This is a dermoscopic photograph of a skin lesion — 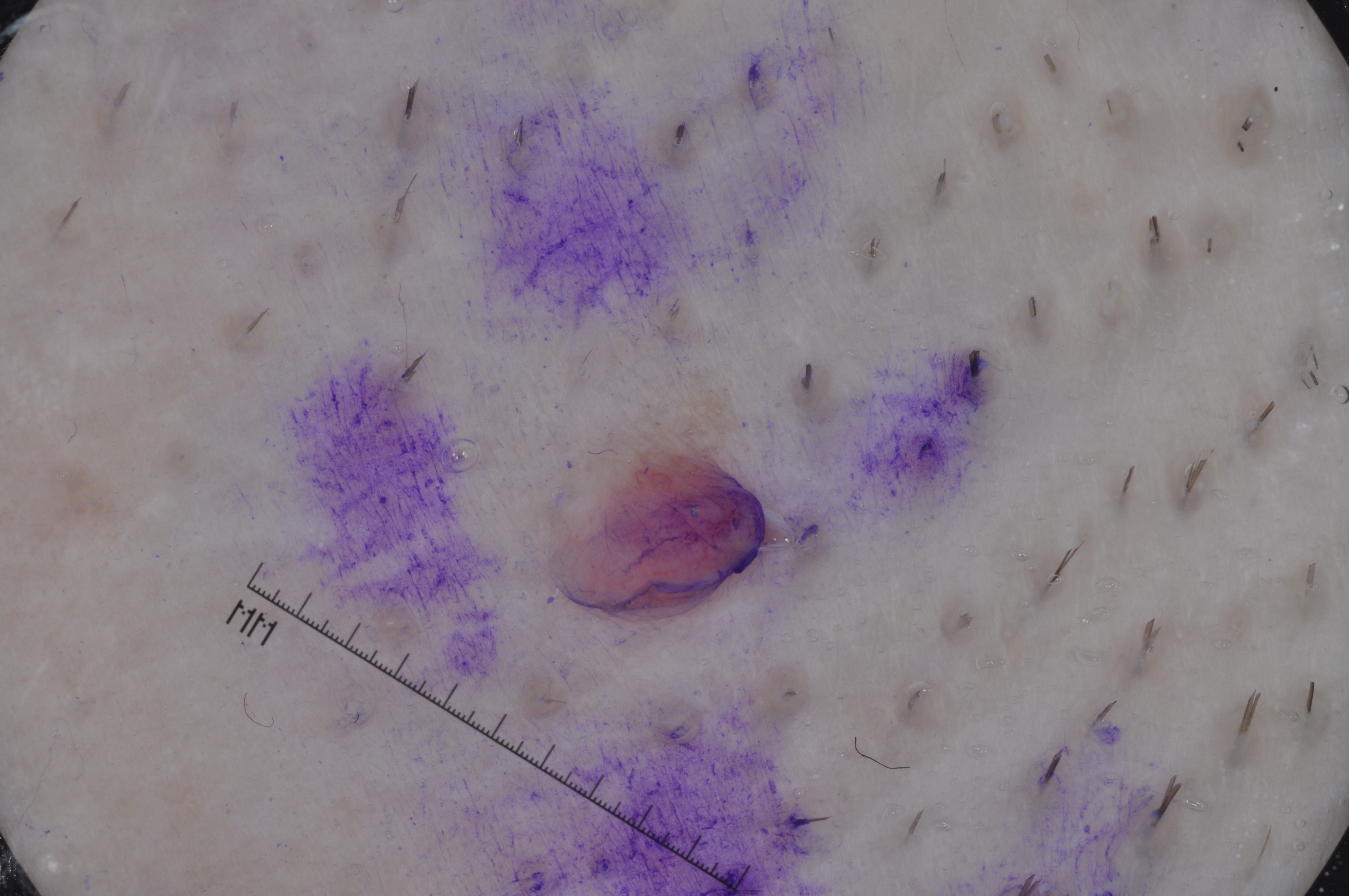{"lesion_location": {"bbox_xyxy": [519, 435, 771, 630]}, "dermoscopic_features": {"present": [], "absent": ["negative network", "pigment network", "milia-like cysts", "streaks"]}, "diagnosis": {"name": "melanocytic nevus", "malignancy": "benign", "lineage": "melanocytic", "provenance": "clinical"}}